This is a close-up image:
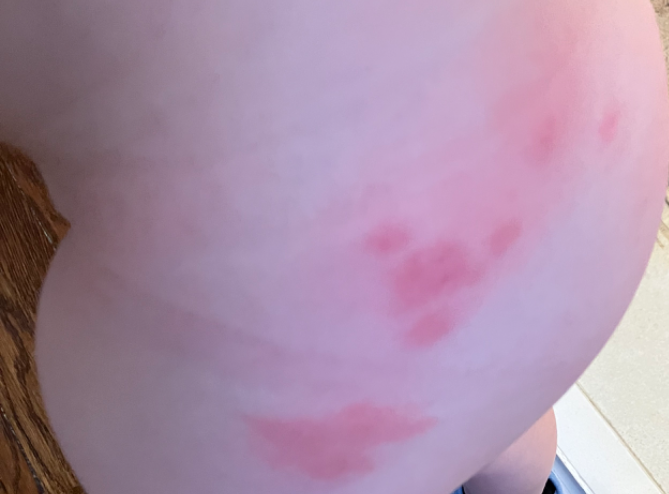Findings: The case was difficult to assess from the available photograph.